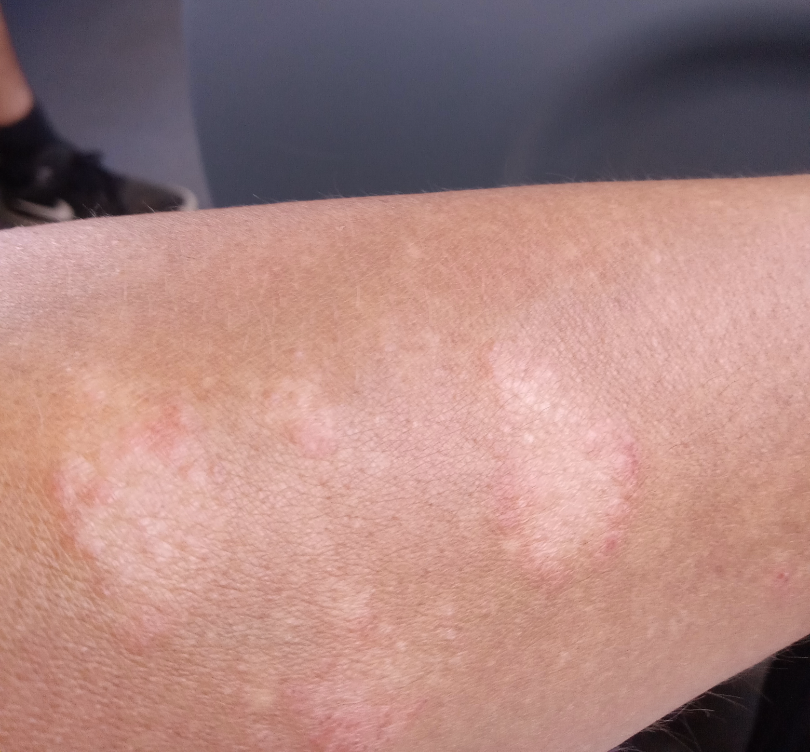| key | value |
|---|---|
| diagnostic considerations | most consistent with Tinea; also on the differential is Granuloma annulare; less likely is Eczema |